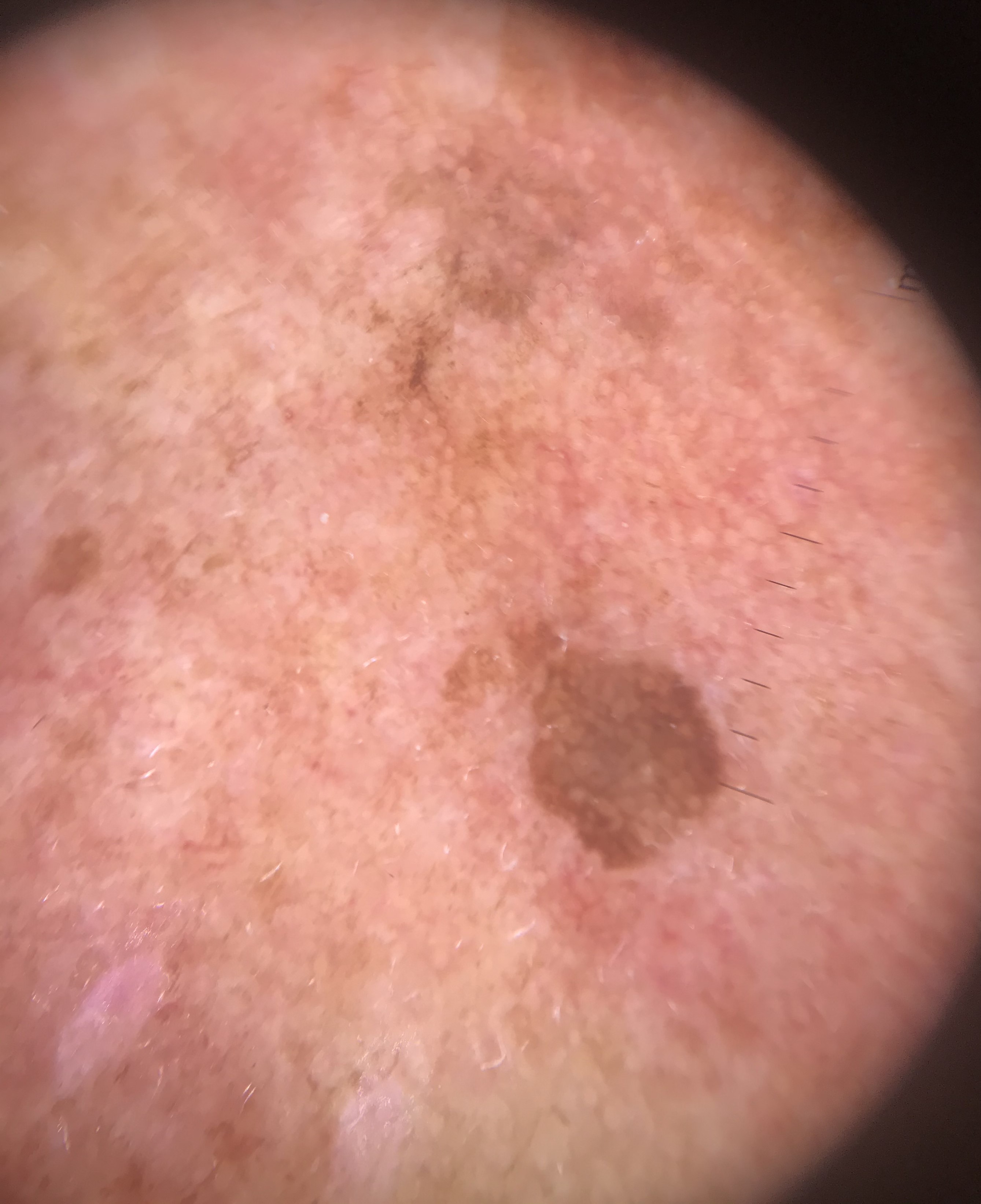Impression: The diagnostic label was a benign lesion — a seborrheic keratosis.